Reported duration is one to three months · the patient described the issue as a rash · the photograph was taken at a distance · the patient reports the lesion is flat and fluid-filled · the patient reports pain and enlargement · lay graders estimated Monk skin tone scale 2 or 4 (two reviewer pools disagreed) · associated systemic symptoms include joint pain and fatigue · located on the leg, top or side of the foot and head or neck:
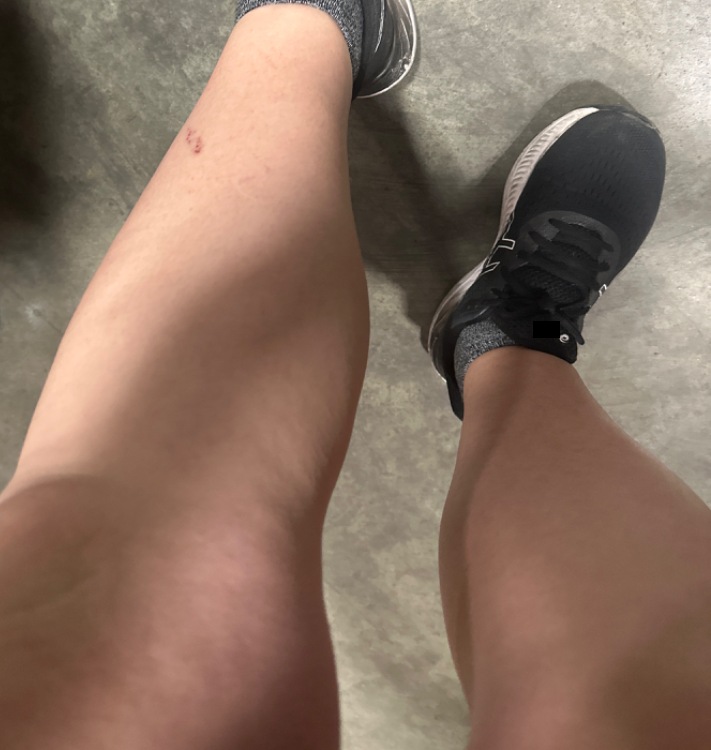The case was difficult to assess from the available photograph.